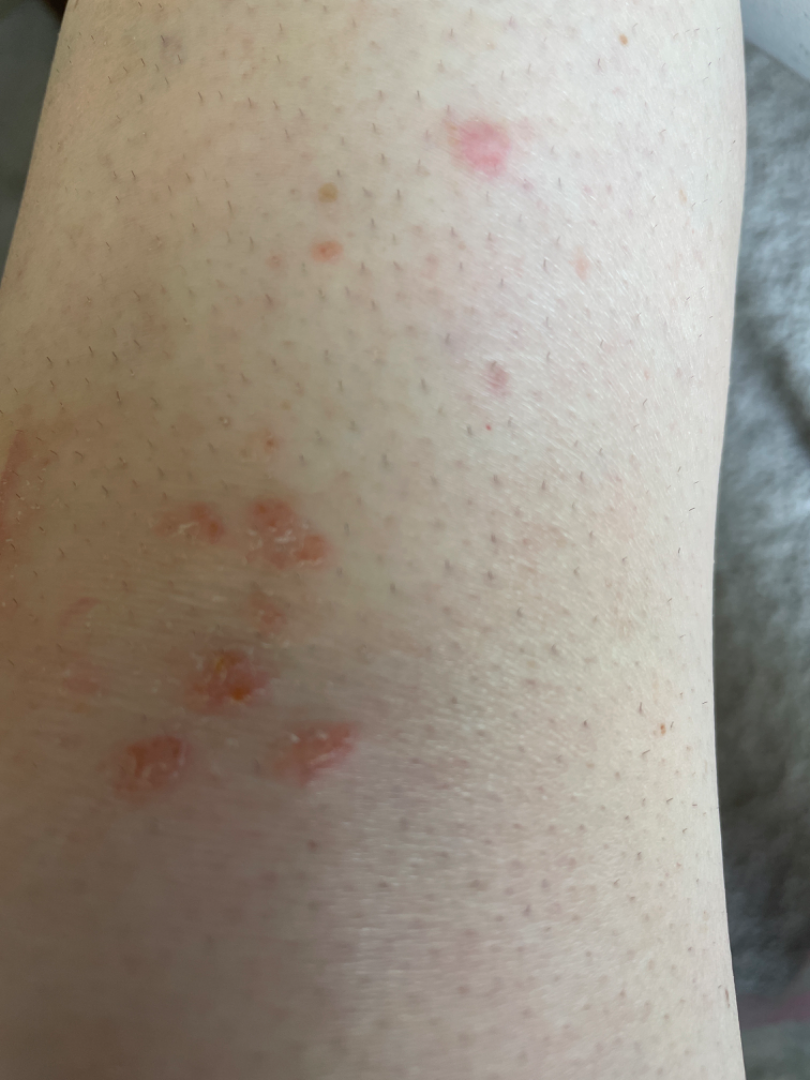| key | value |
|---|---|
| assessment | unable to determine |
| shot type | close-up |